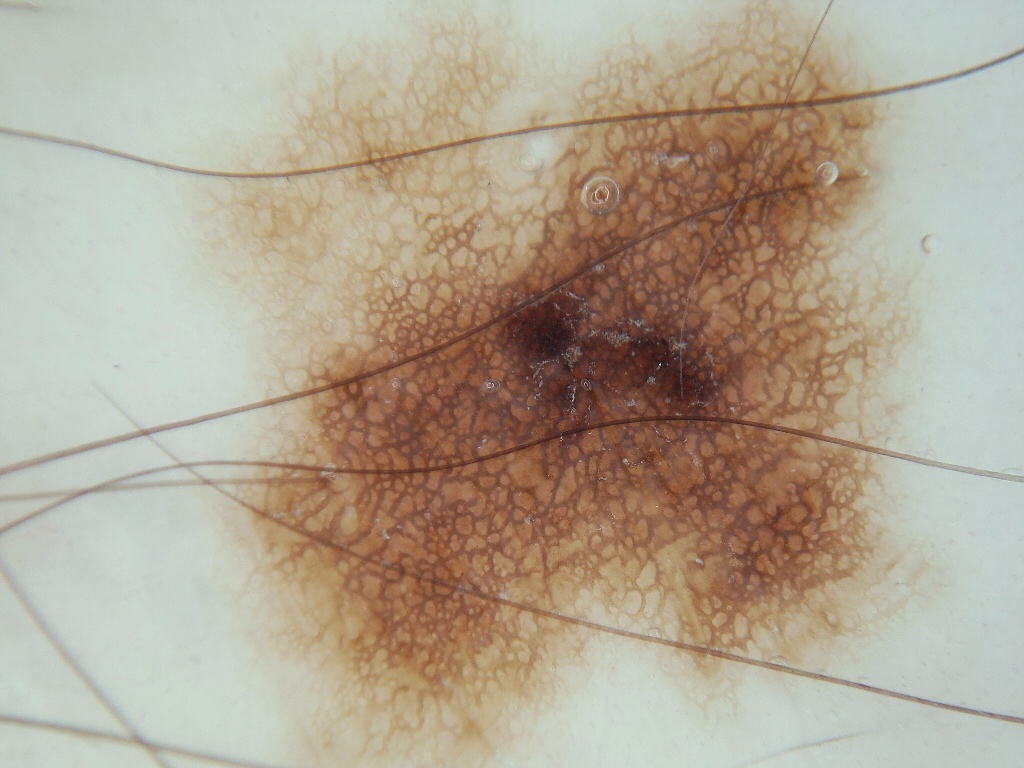A skin lesion imaged with a dermatoscope. The lesion is located at left=166, top=4, right=971, bottom=766. The lesion was assessed as a benign lesion.